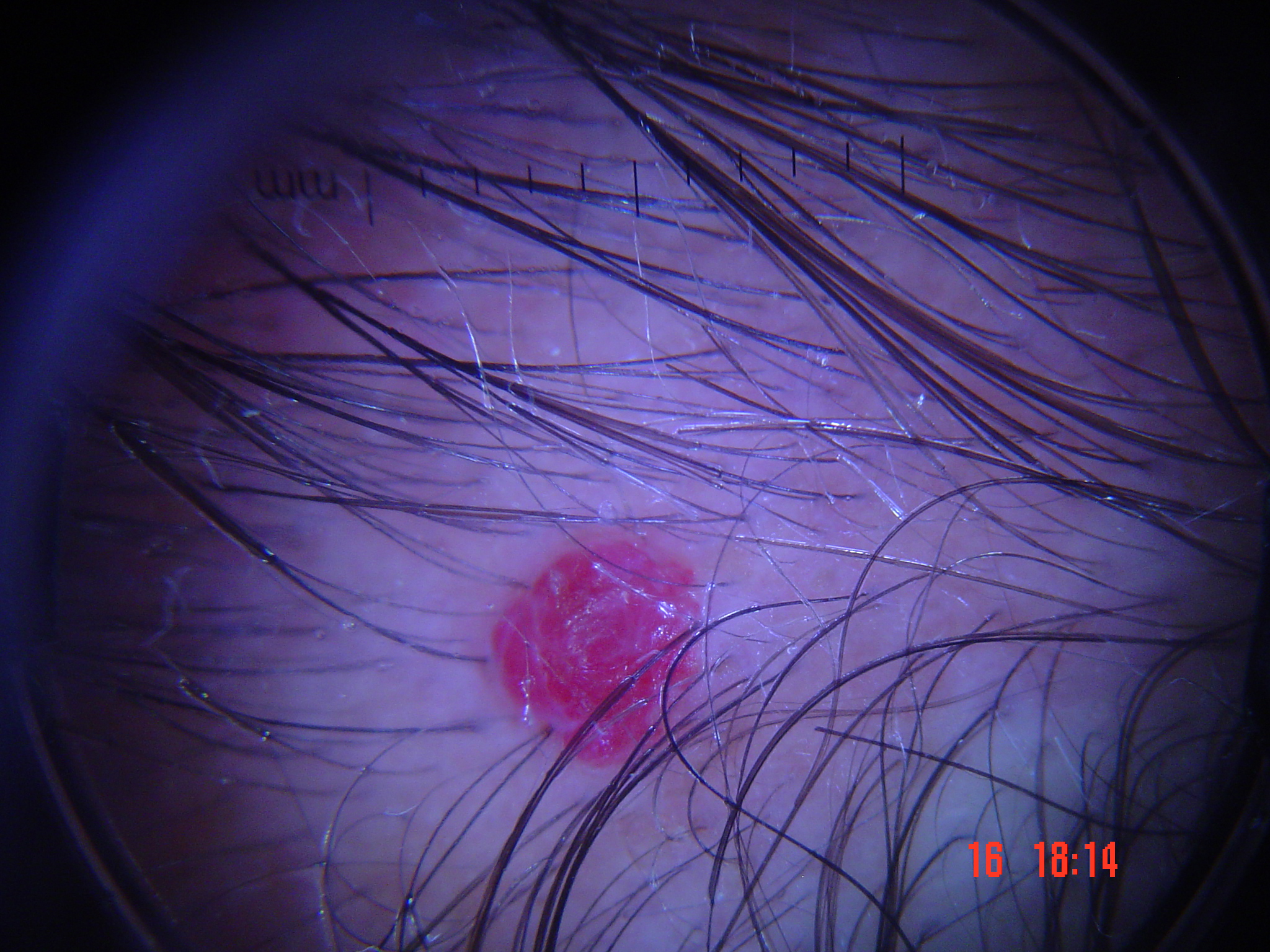Q: What kind of image is this?
A: dermatoscopy
Q: What is the lesion category?
A: vascular
Q: What was the diagnostic impression?
A: hemangioma (expert consensus)